A female subject in their 70s. A clinical photograph of a skin lesion. The patient is FST II: 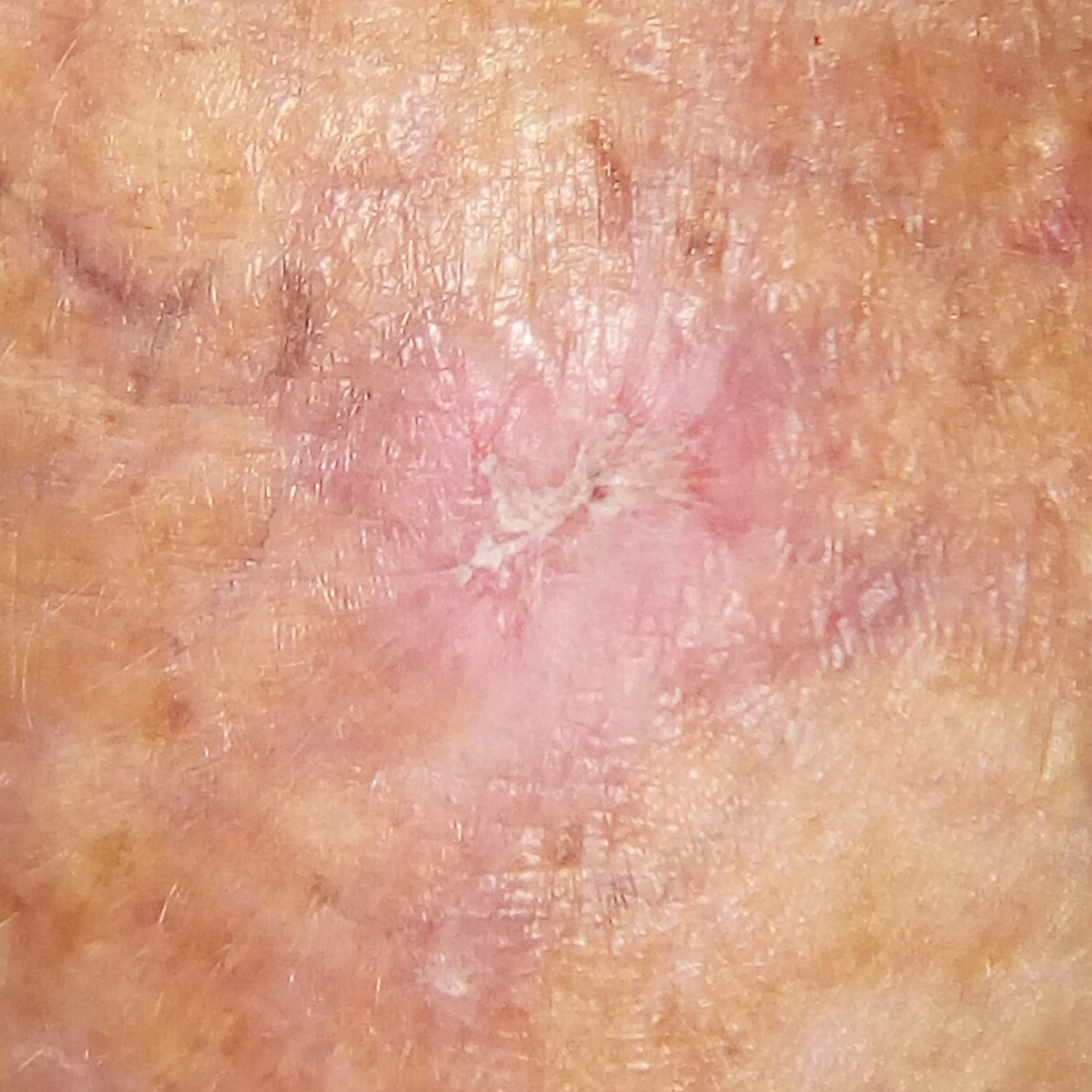<record>
  <lesion_location>a forearm</lesion_location>
  <lesion_size>
    <diameter_1_mm>12.0</diameter_1_mm>
    <diameter_2_mm>10.0</diameter_2_mm>
  </lesion_size>
  <symptoms>none reported</symptoms>
  <diagnosis>
    <name>actinic keratosis</name>
    <code>ACK</code>
    <malignancy>indeterminate</malignancy>
    <confirmation>histopathology</confirmation>
  </diagnosis>
</record>